A female patient aged around 45. A dermoscopy image of a single skin lesion.
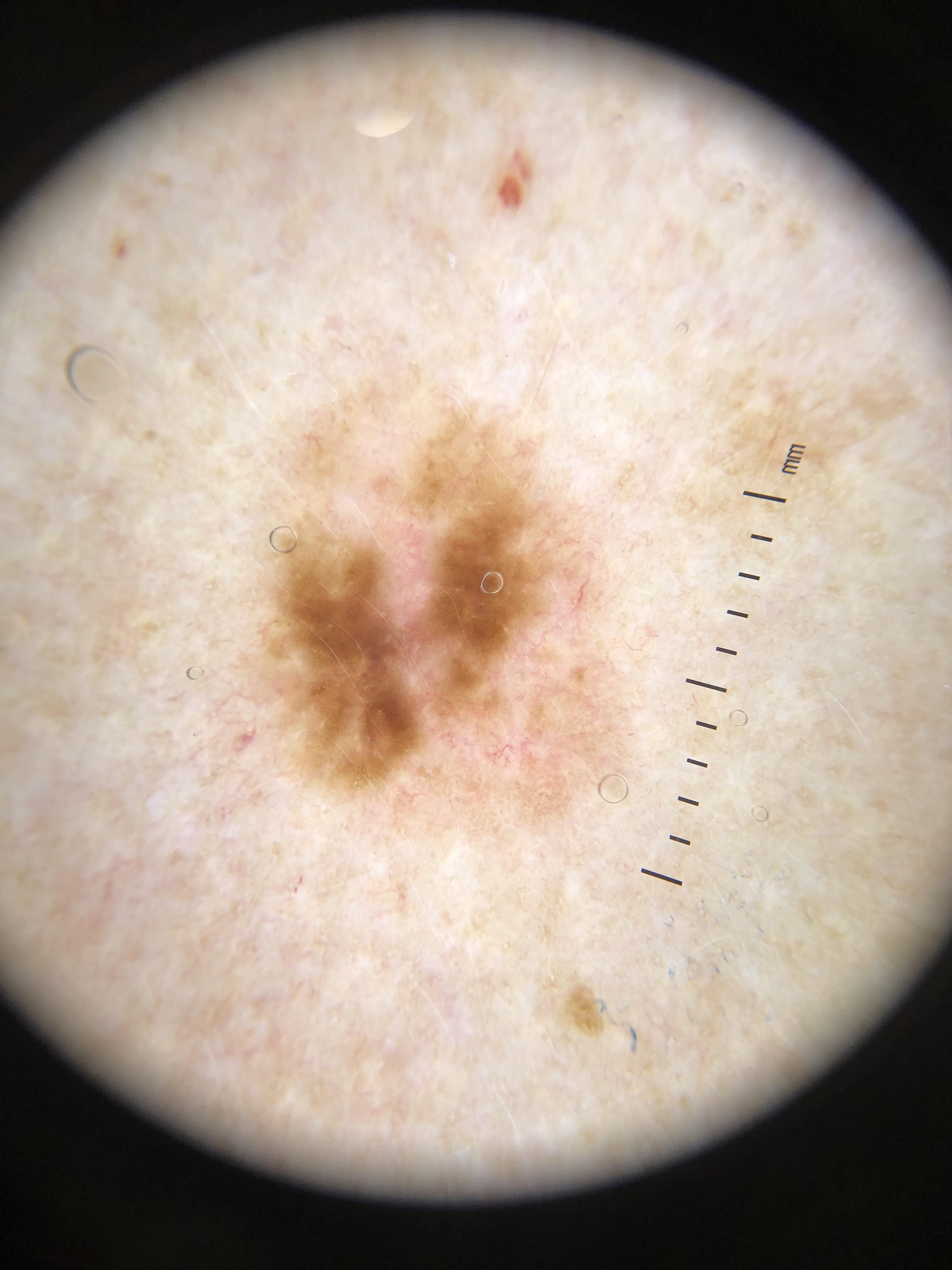pathology = Nevus (biopsy-proven).